A dermoscopic image of a skin lesion — 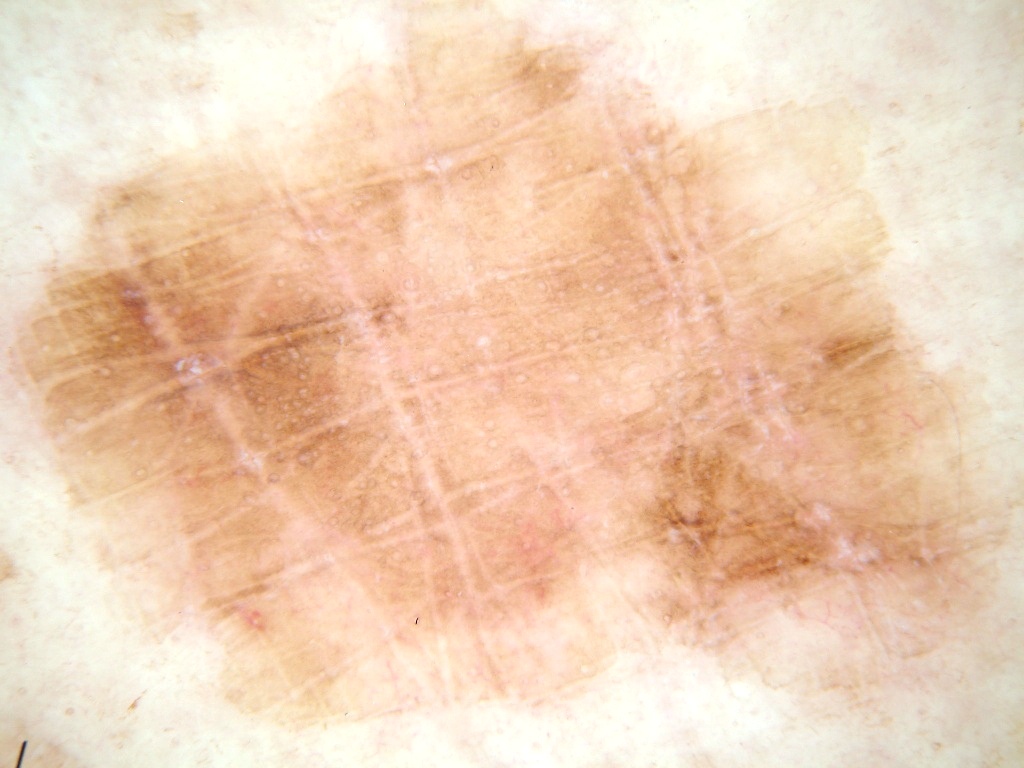<dermoscopy>
  <lesion_location>spans the dermoscopic field</lesion_location>
  <dermoscopic_features>
    <present/>
    <absent>streaks, globules</absent>
  </dermoscopic_features>
  <diagnosis>
    <malignancy>benign</malignancy>
    <provenance>clinical</provenance>
  </diagnosis>
</dermoscopy>